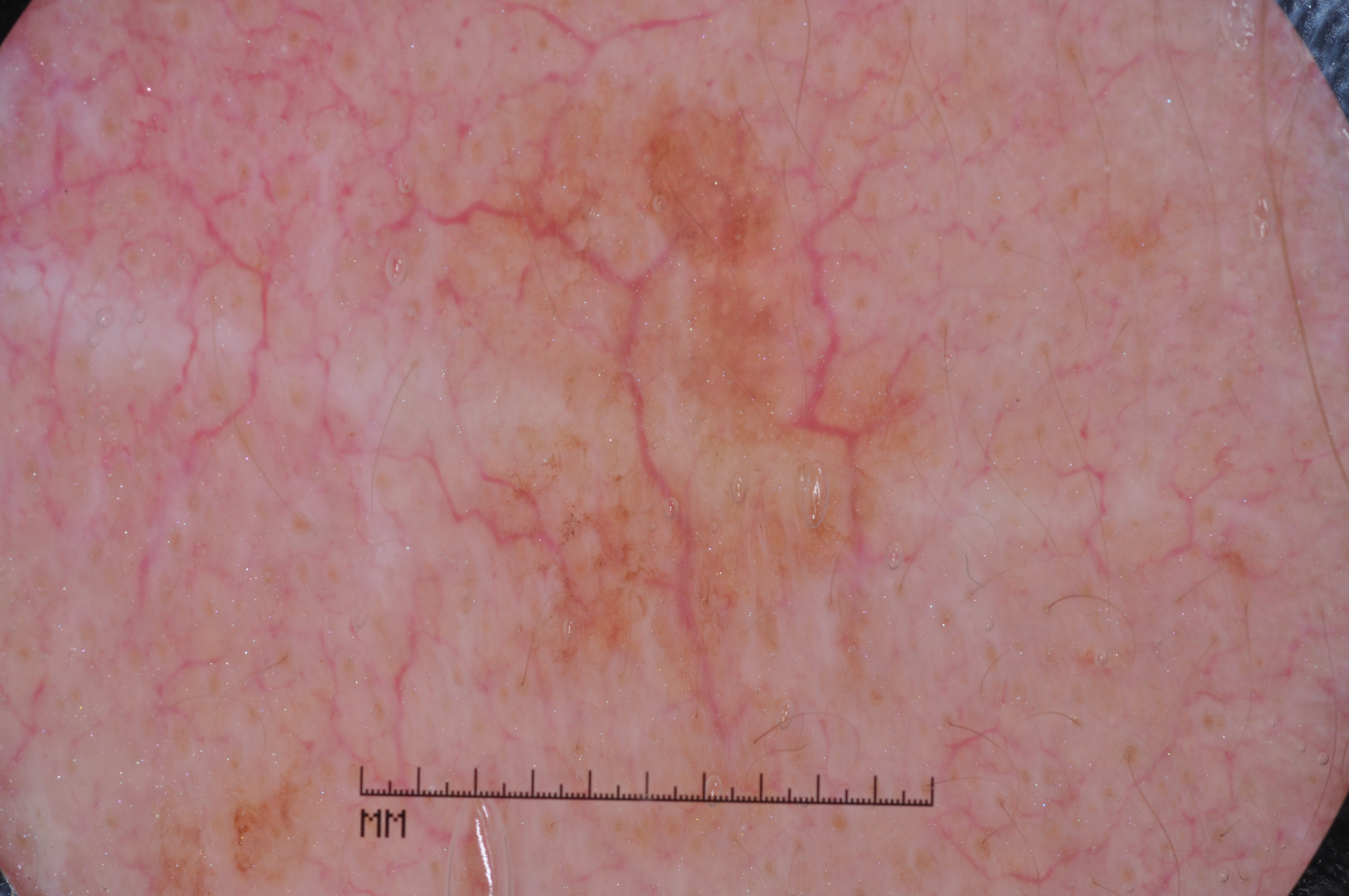Case summary:
– image type — dermatoscopic image of a skin lesion
– bounding box — x1=346 y1=57 x2=964 y2=887
– diagnostic label — a melanoma